A dermoscopic view of a skin lesion.
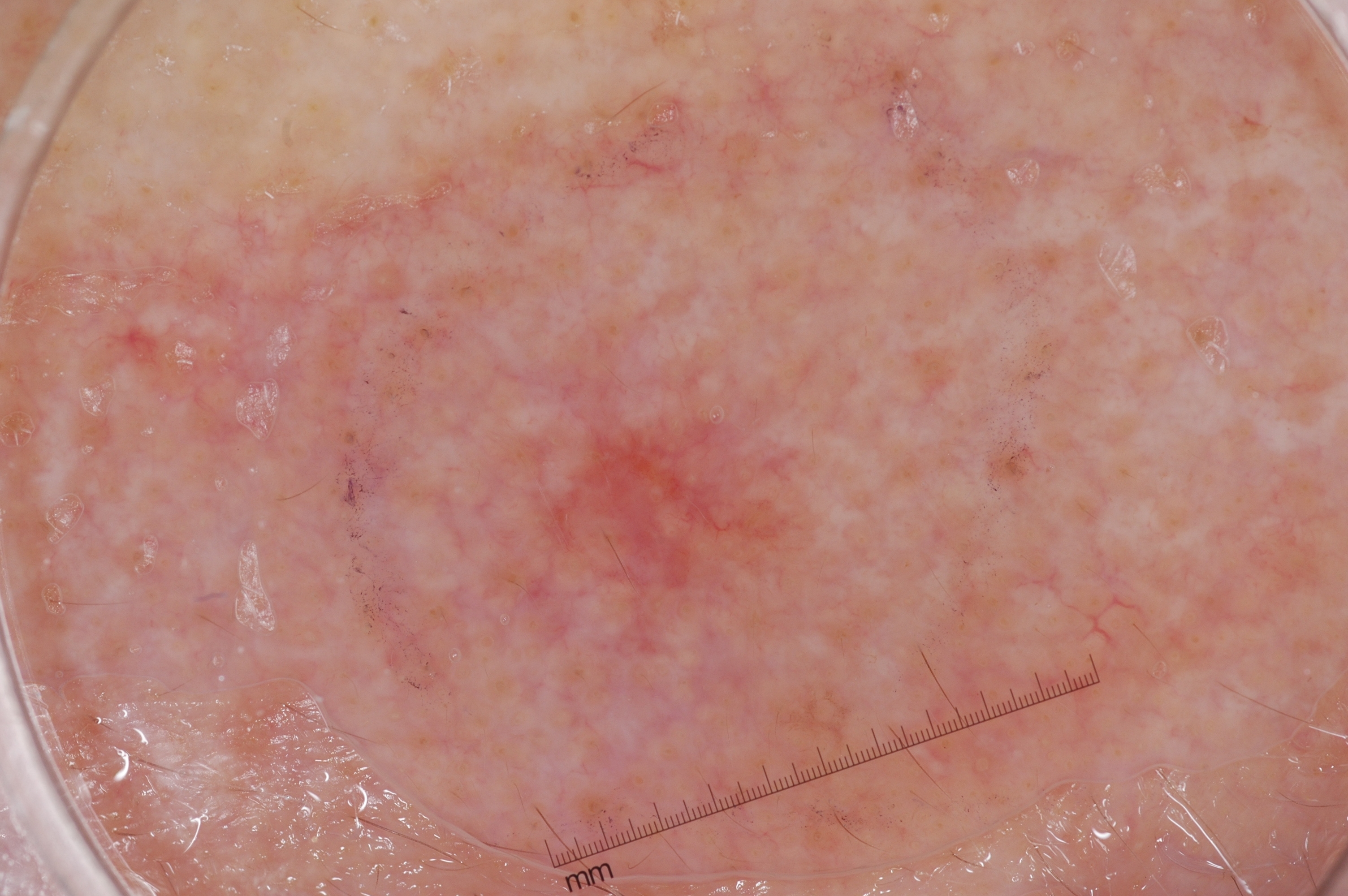absent dermoscopic findings: milia-like cysts, pigment network, streaks, and negative network
location: 515 414 814 609
extent: small
impression: a seborrheic keratosis, a benign skin lesion